A male patient age 80. The patient was assessed as Fitzpatrick skin type II. A smartphone photograph of a skin lesion. The chart notes prior malignancy (patient or family), pesticide exposure, and alcohol use:
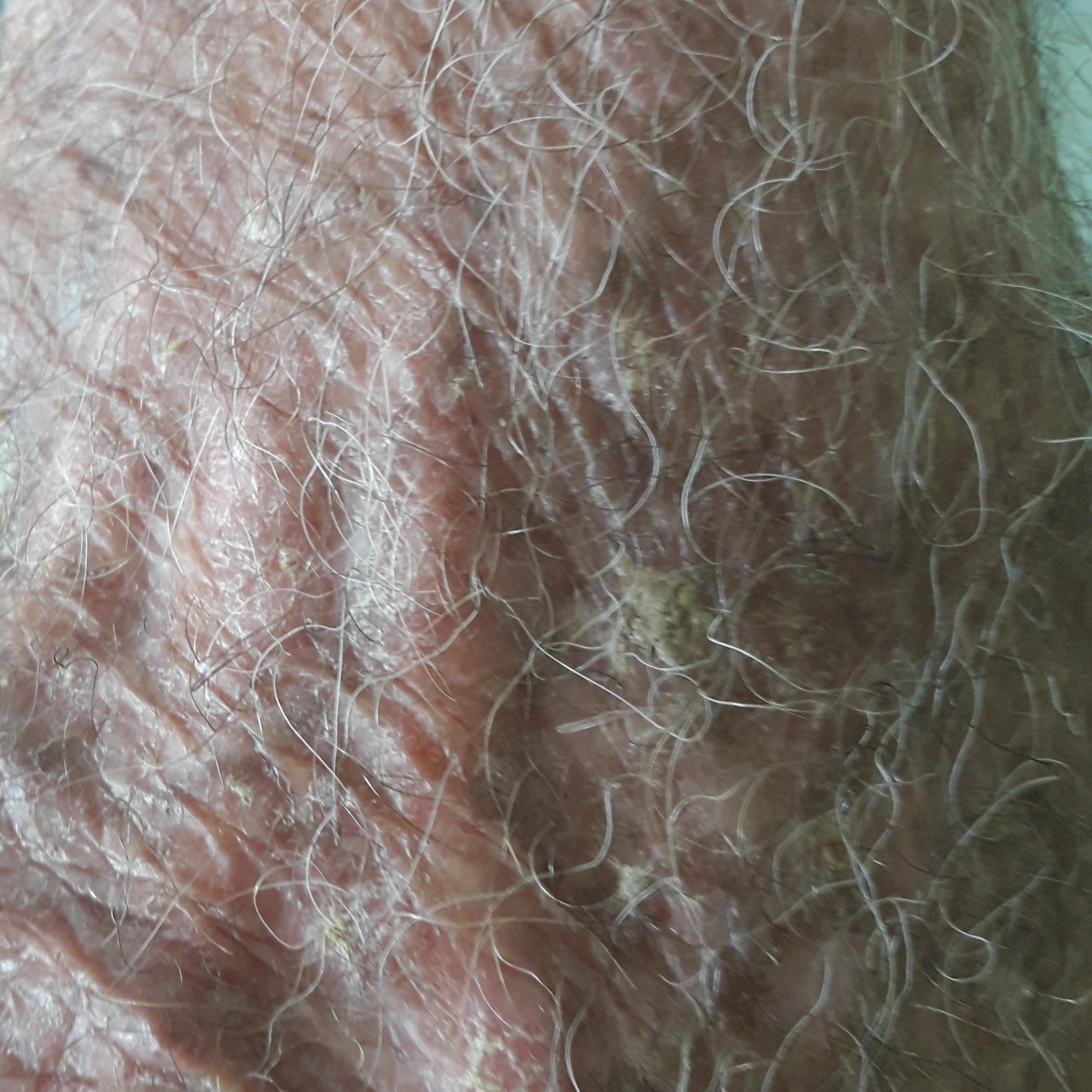• diameter — 3x2 mm
• reported symptoms — elevation
• assessment — actinic keratosis (clinical consensus)